The lesion involves the sole of the foot and top or side of the foot. This image was taken at an angle. The subject is female:
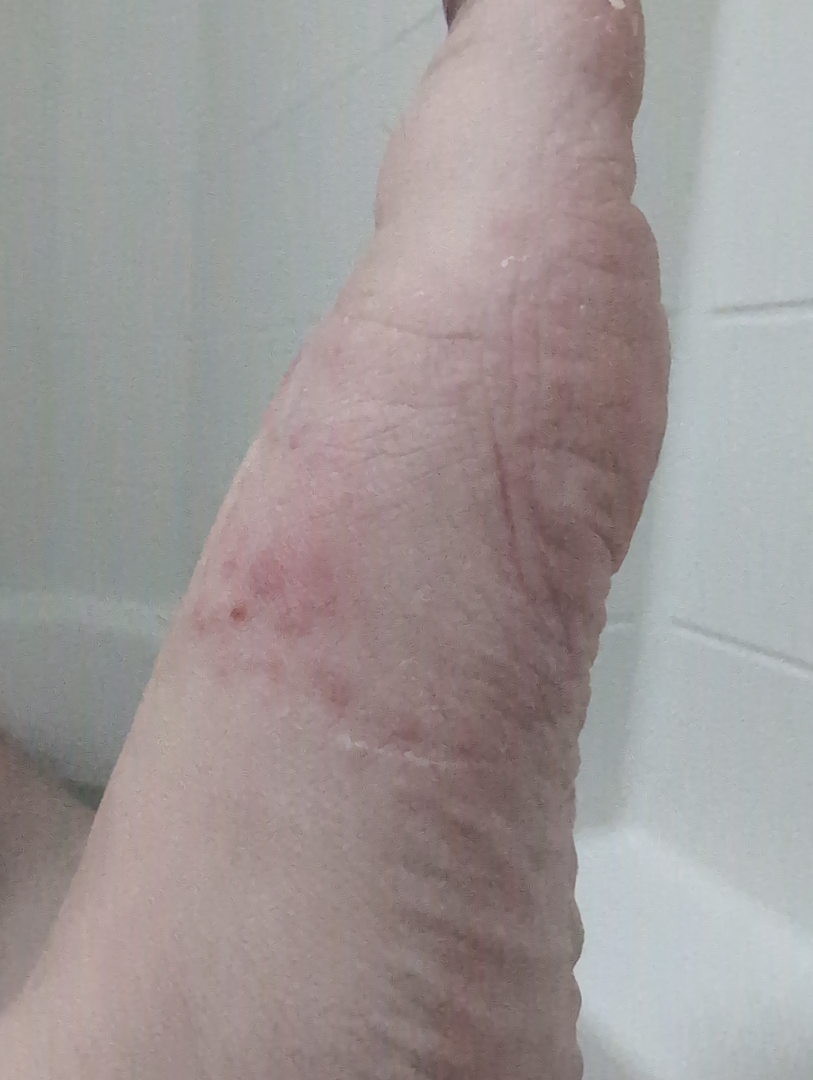{"differential": {"leading": ["Eczema"]}}